The affected area is the top or side of the foot. The photograph is a close-up of the affected area:
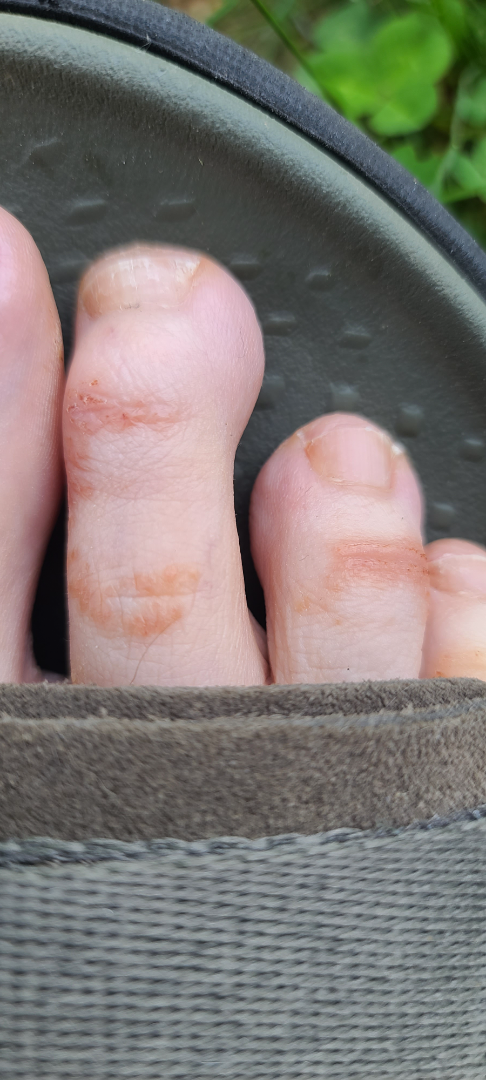impression = one reviewing dermatologist: the differential is split between Impetigo, Eczema and Allergic Contact Dermatitis.